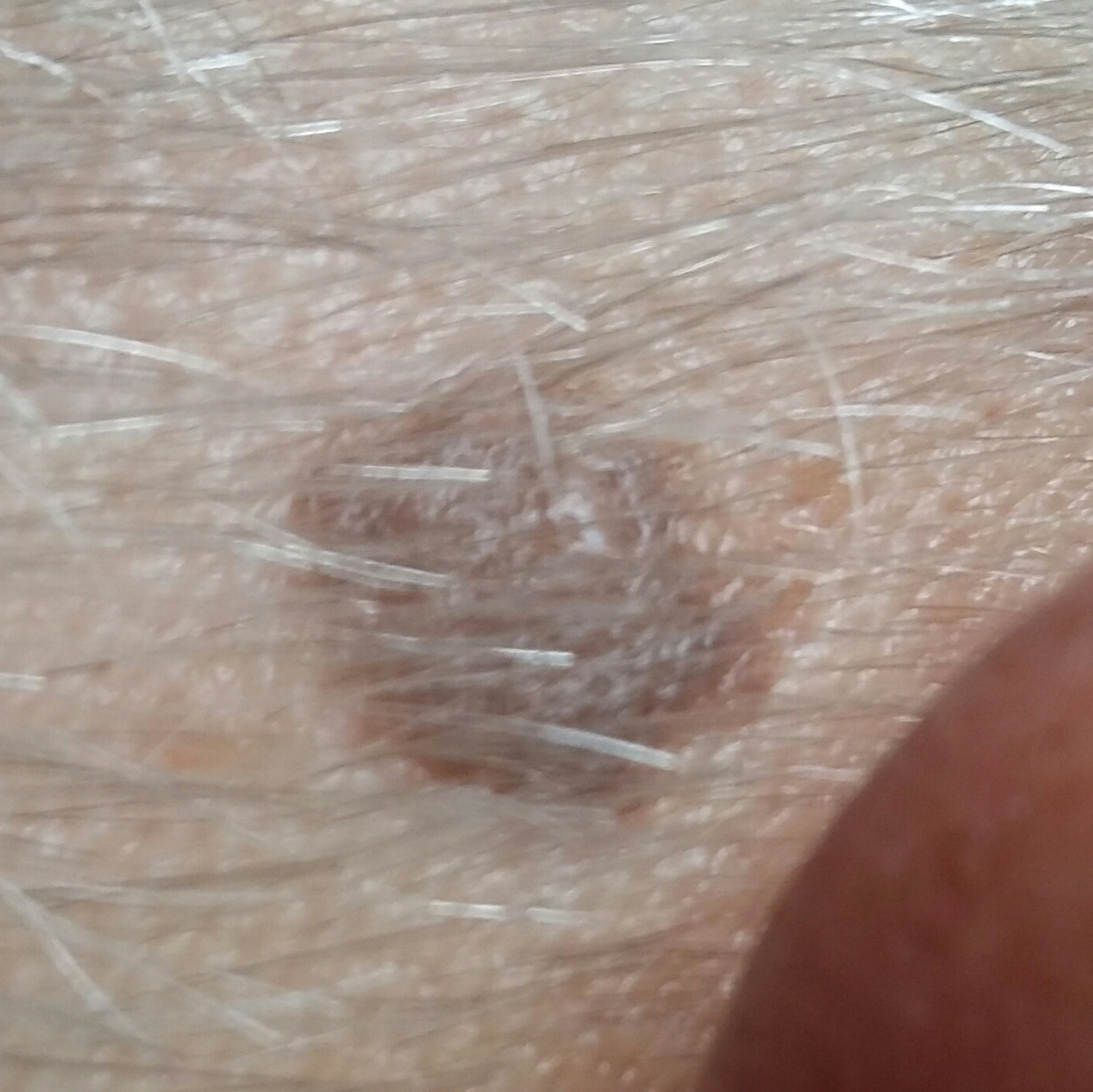subject = 75 years of age | modality = smartphone clinical photo | reported symptoms = elevation | assessment = seborrheic keratosis (clinical consensus).